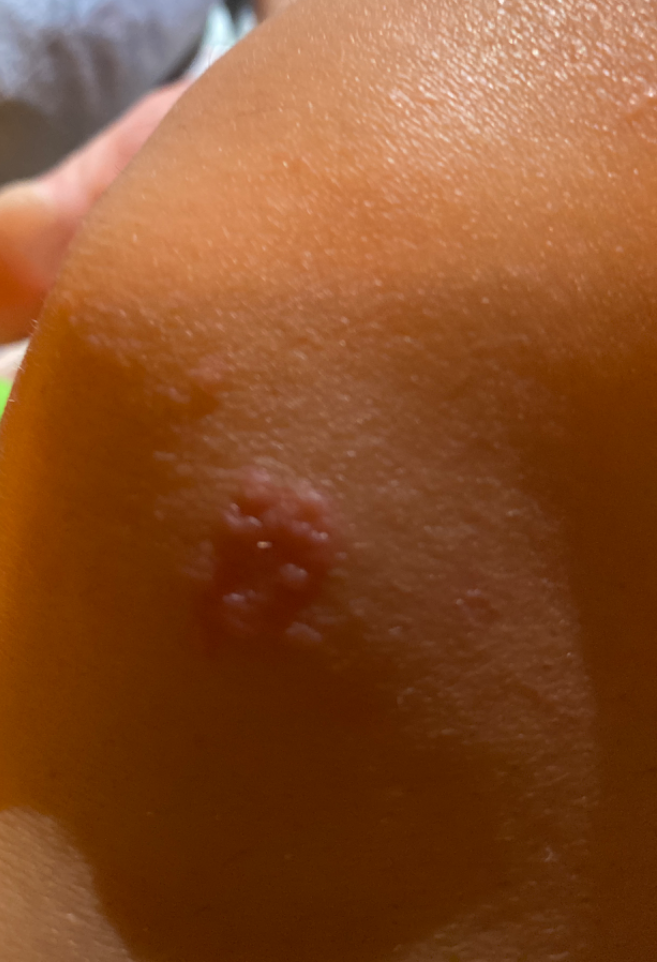Case summary:
* assessment: could not be assessed